No constitutional symptoms were reported, the lesion is associated with itching, skin tone: Fitzpatrick phototype V, this image was taken at an angle, the condition has been present for more than one year, the patient considered this a rash:
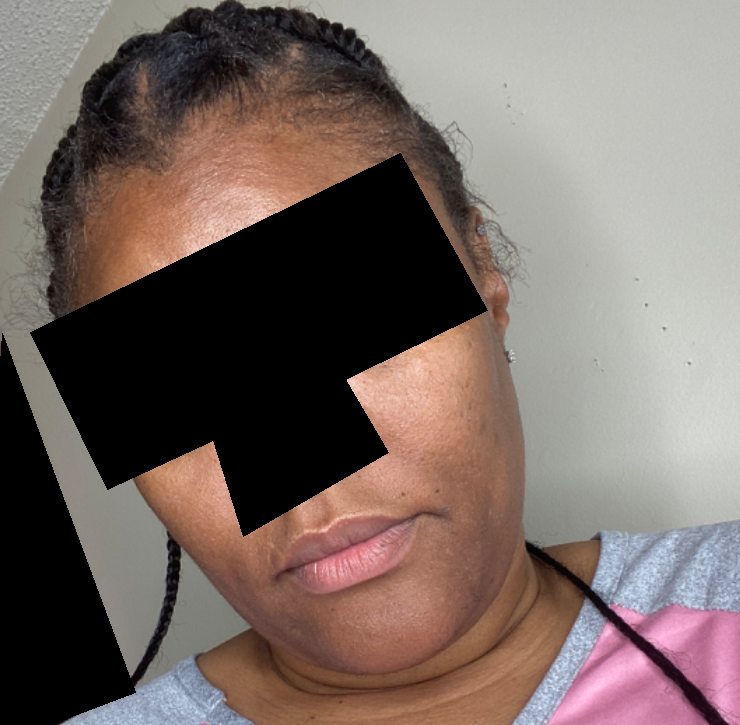Findings:
No discernible pathology was noted by the reviewing dermatologist.